Skin tone: Fitzpatrick III · the photograph is a close-up of the affected area · texture is reported as flat.
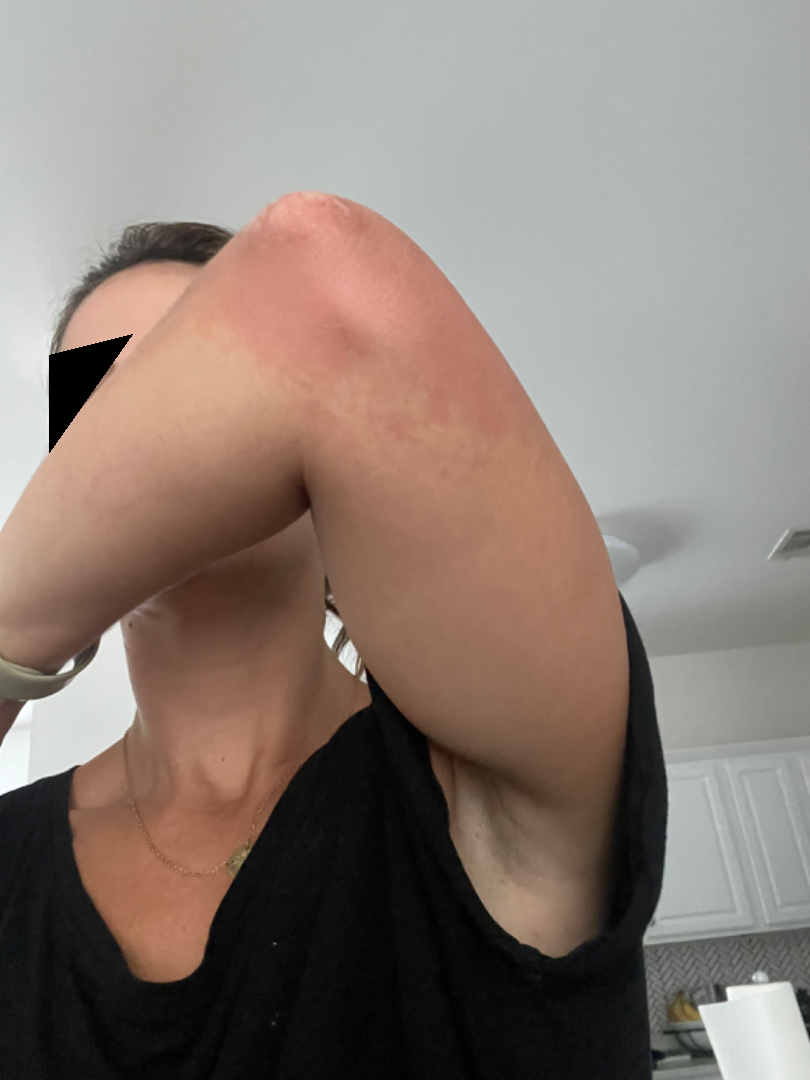The favored diagnosis is Urticaria; the differential also includes Cellulitis; also raised was Eczema.